A dermoscopy image of a single skin lesion.
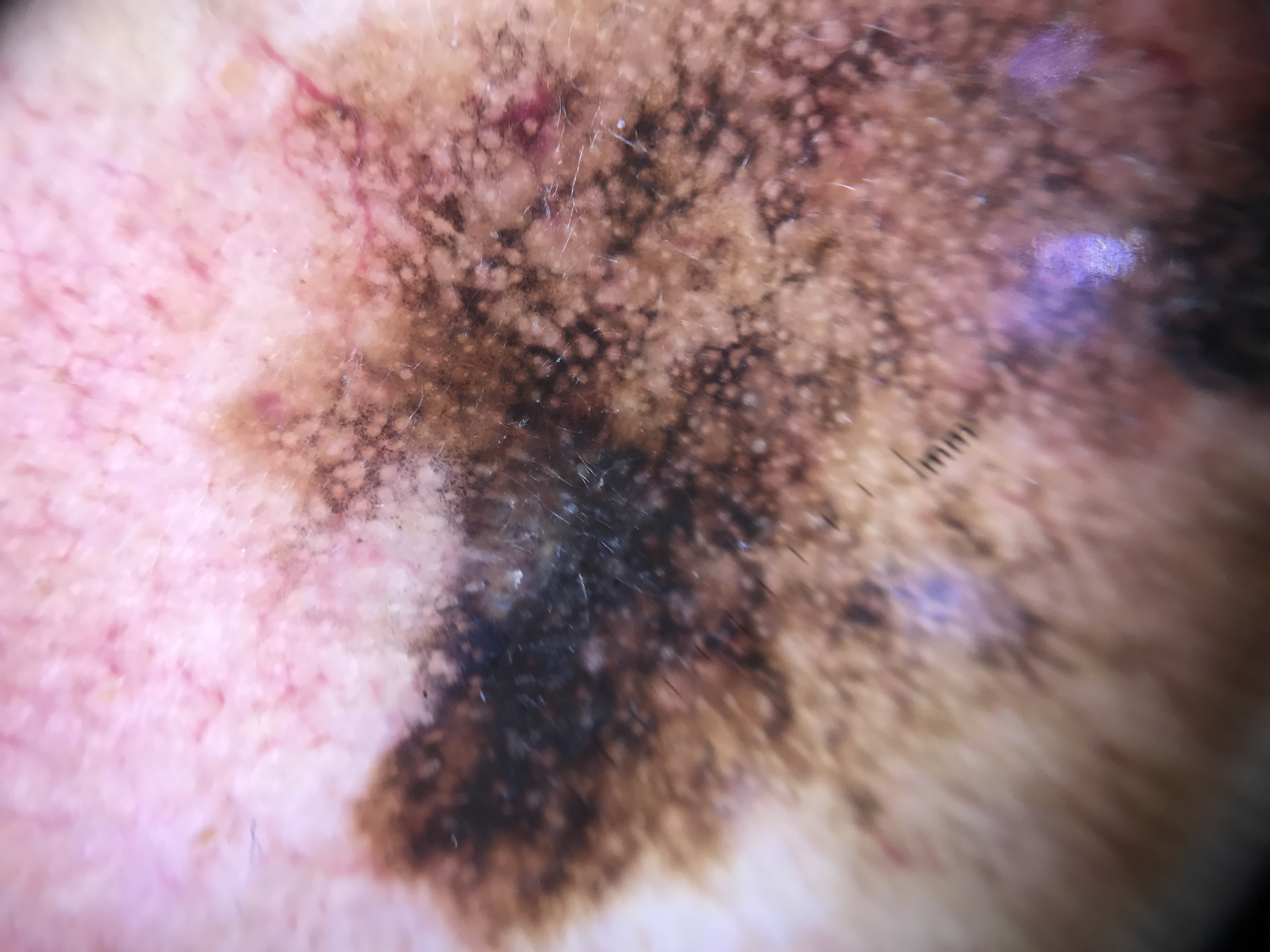Conclusion:
Histopathologically confirmed as a lentigo maligna.